A dermoscopic image of a skin lesion: 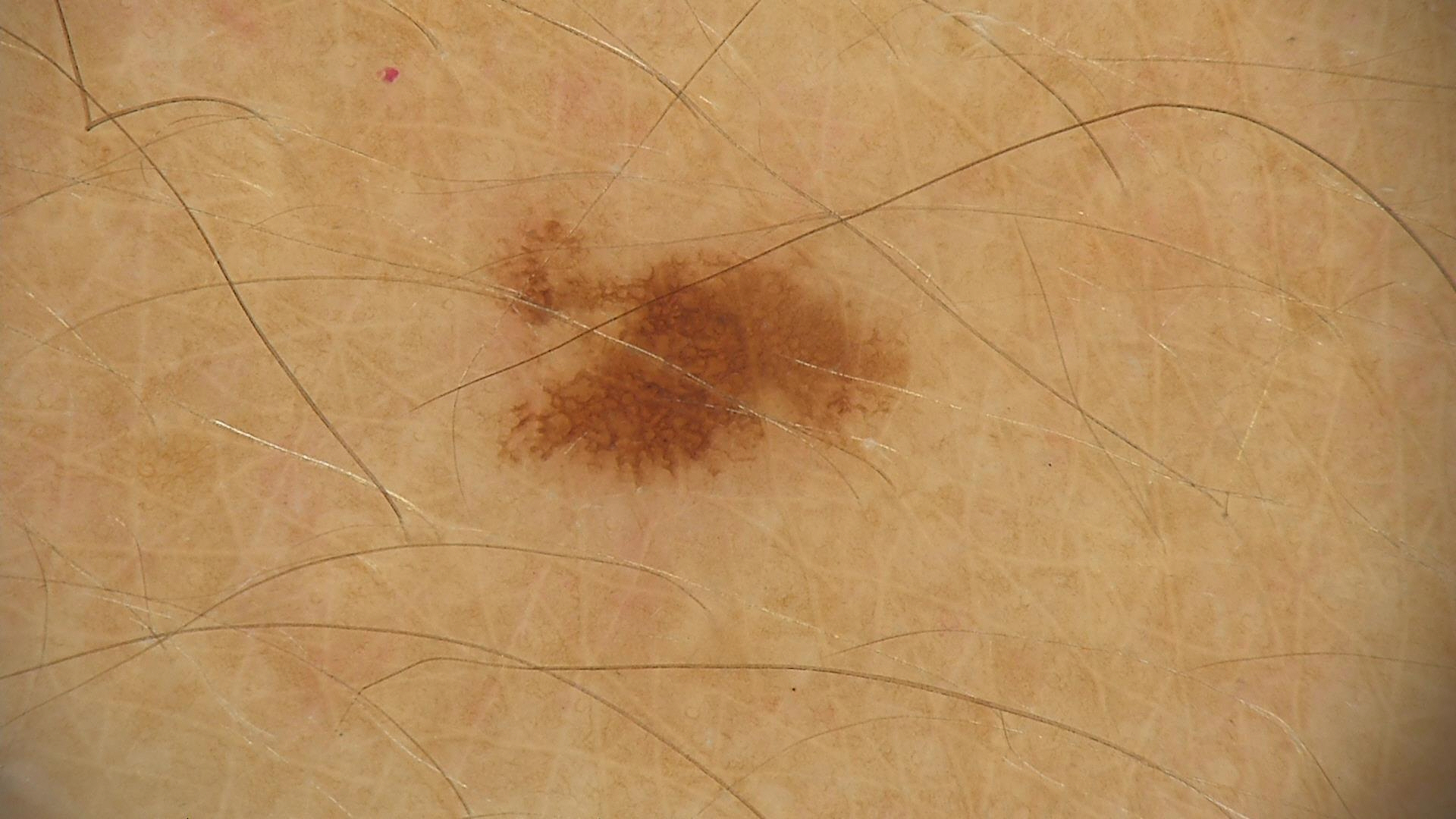Conclusion: The diagnosis was a benign lesion — a dysplastic junctional nevus.